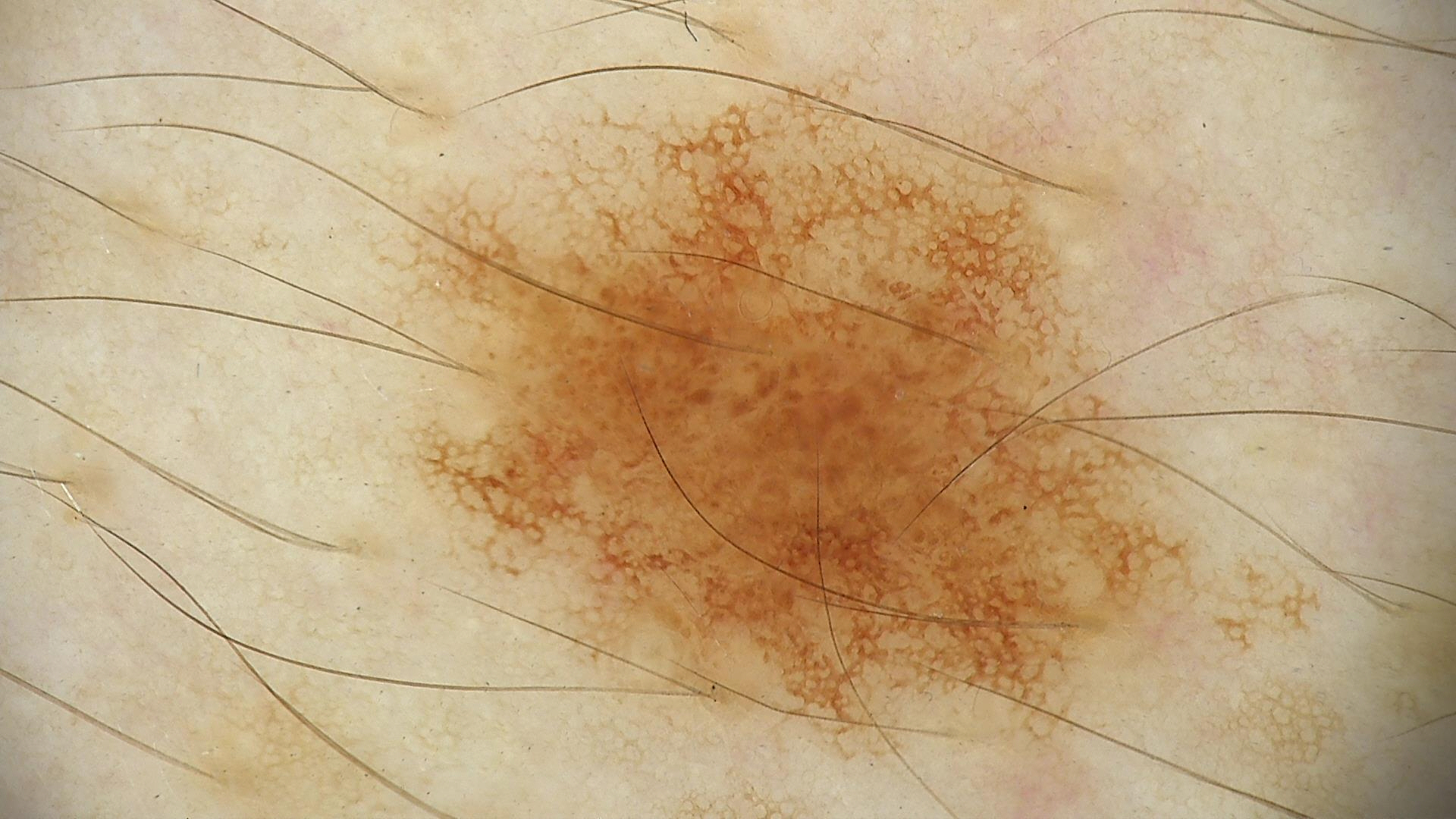Impression:
Consistent with a dysplastic junctional nevus.